The photo was captured at an angle, the lesion involves the arm, the patient is a female aged 30–39.
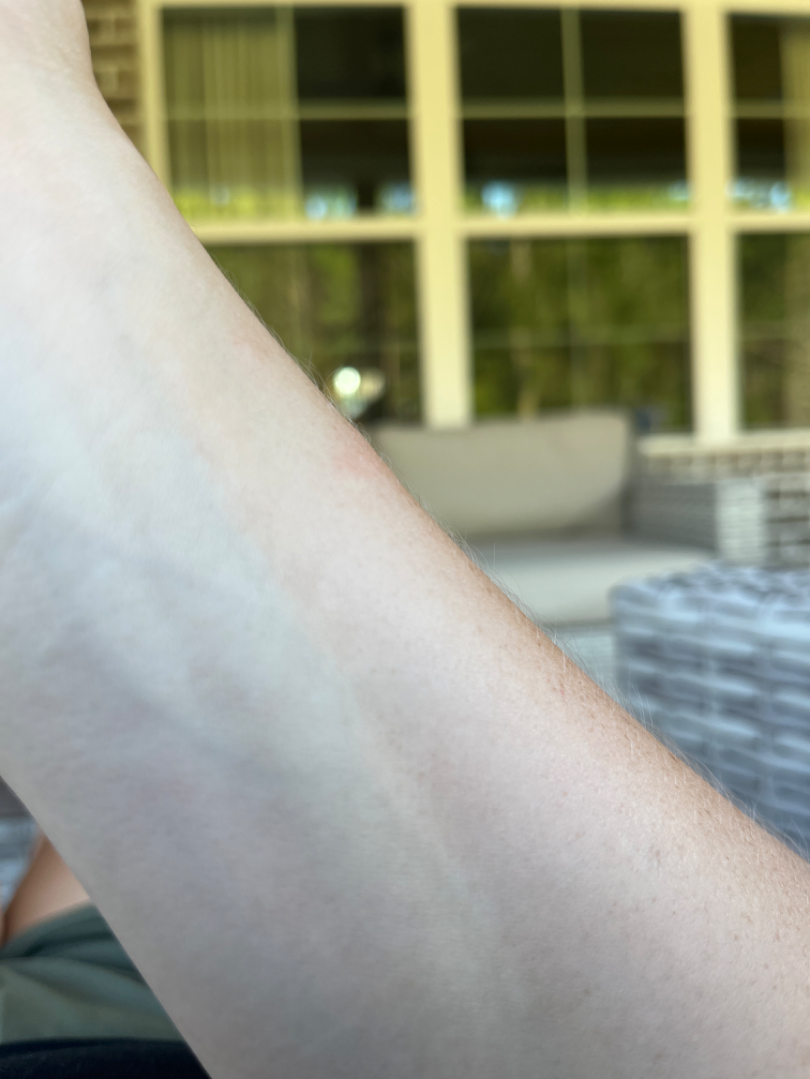clinical impression: Eczema (possible); Allergic Contact Dermatitis (possible)